An image taken at a distance. The lesion involves the leg and top or side of the foot — 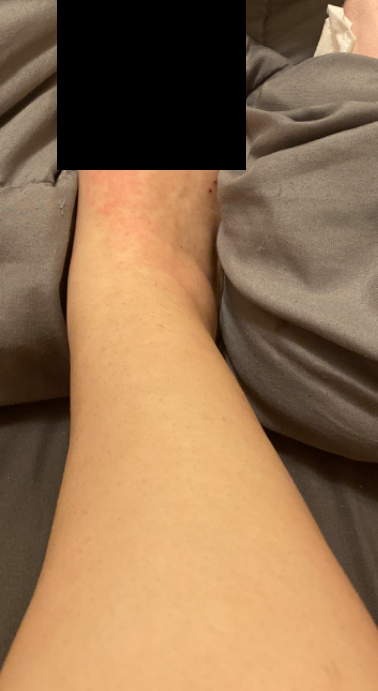The skin condition could not be confidently assessed from this image.